A dermoscopic image of a skin lesion:
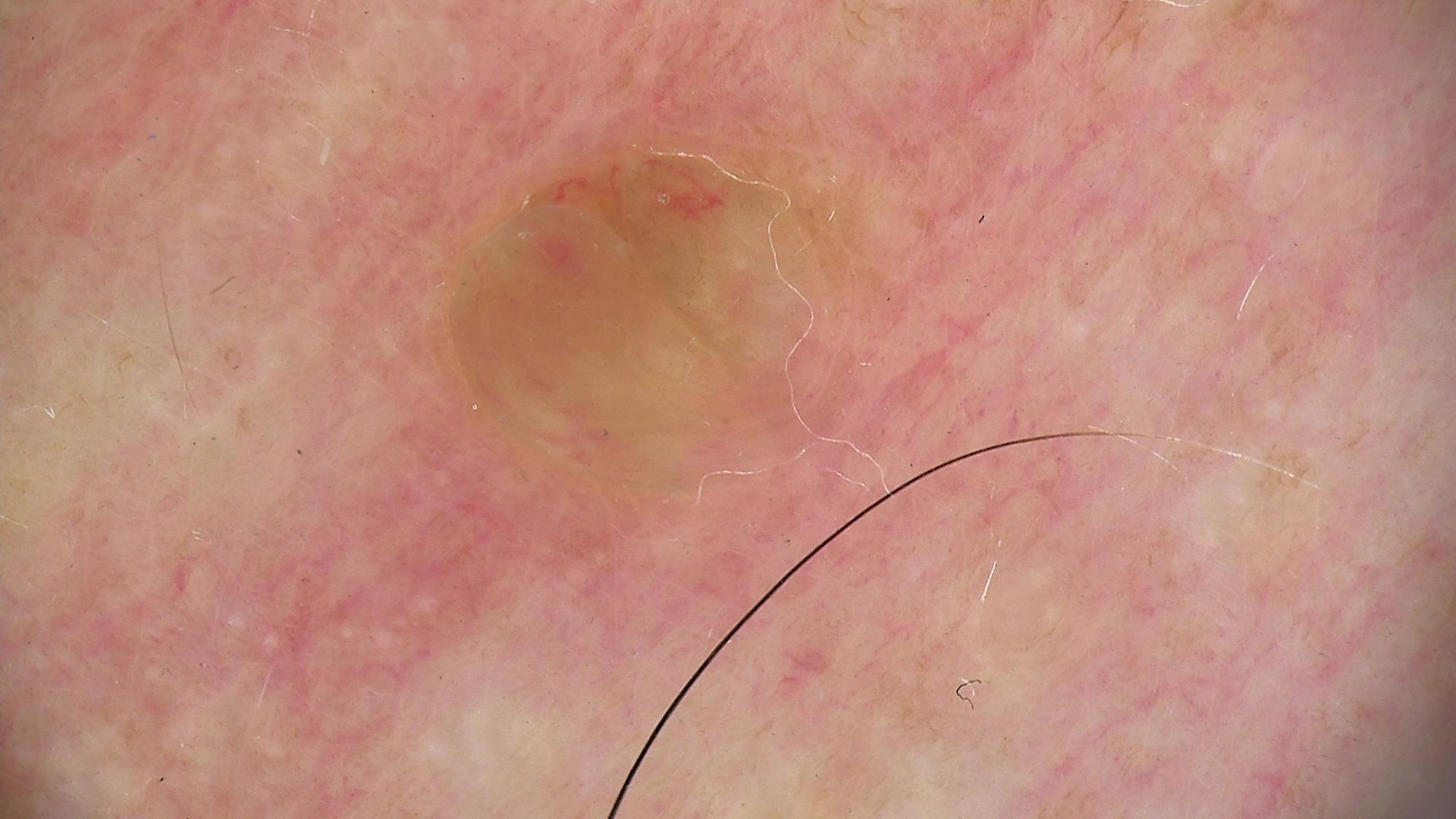This is a banal lesion. Classified as a dermal nevus.